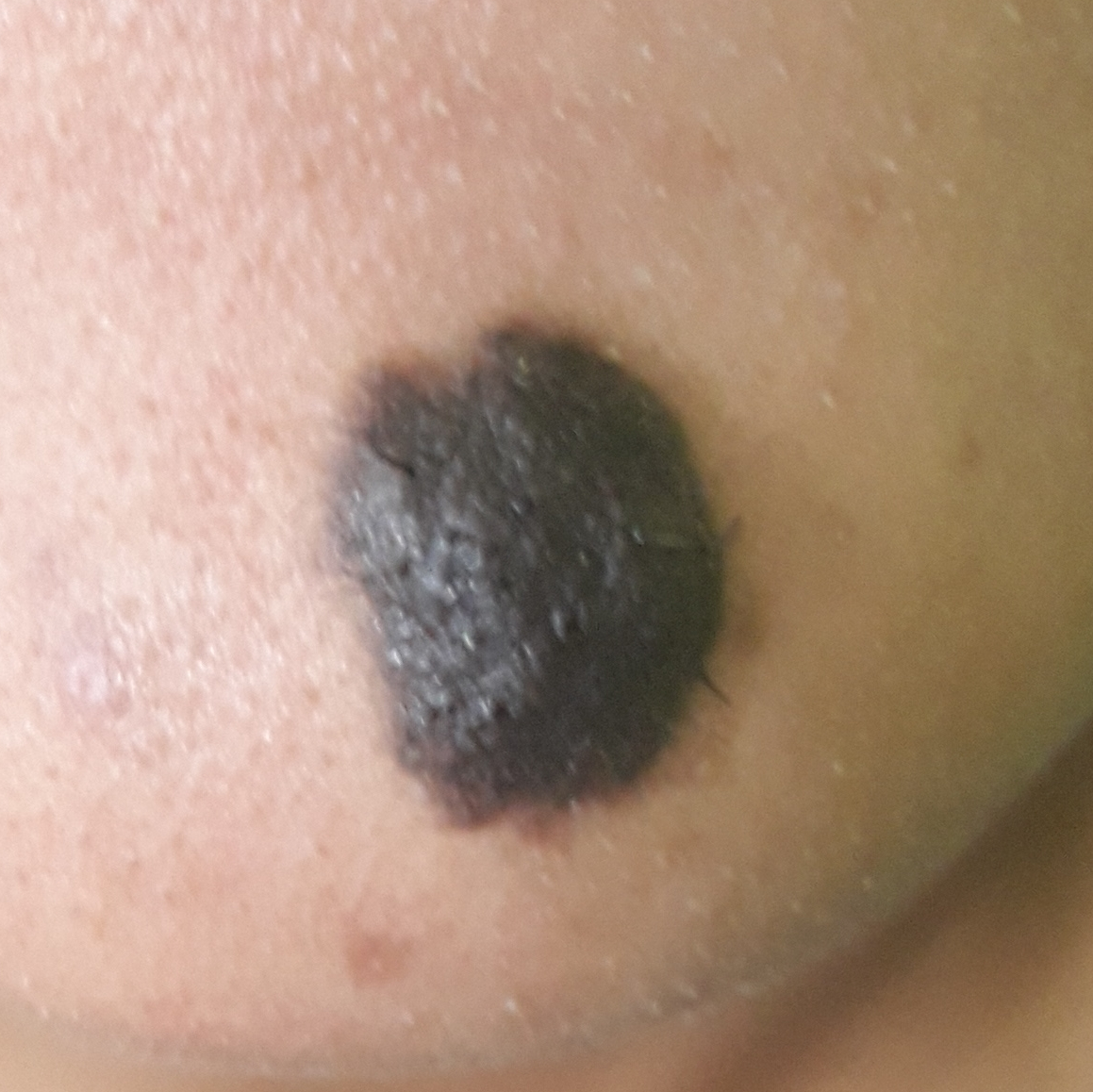modality = clinical photograph | patient = 22 years of age | location = the face | symptoms = growth, elevation | diagnosis = nevus (clinical consensus).